The affected area is the head or neck · the photograph was taken at a distance · the patient is a female aged 50–59 — 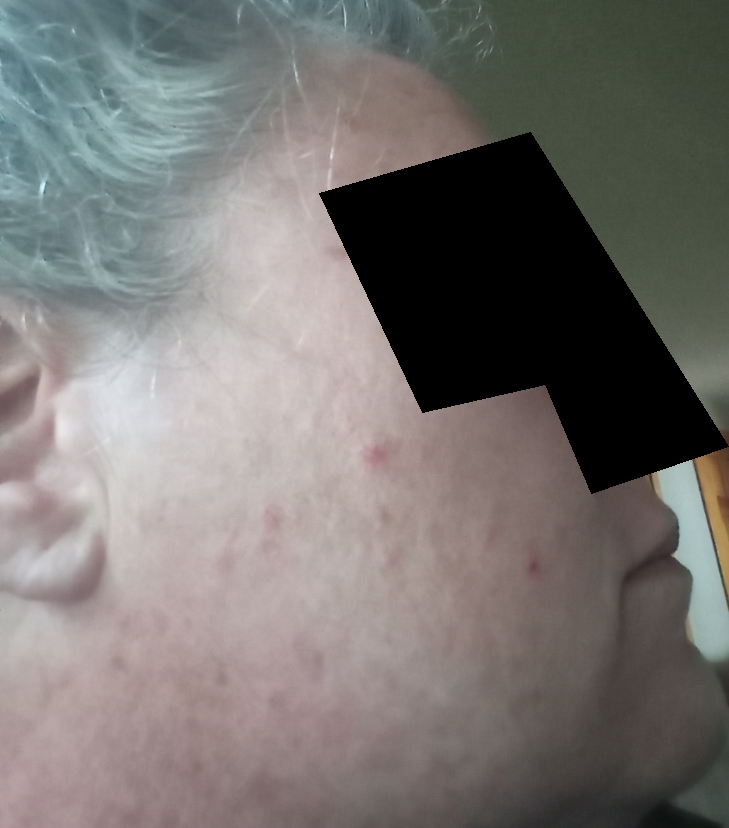Findings:
- skin tone · Fitzpatrick phototype II; lay reviewers estimated Monk Skin Tone 2
- other reported symptoms · mouth sores
- duration · less than one week
- differential diagnosis · a single dermatologist reviewed the case: most consistent with Acne